No associated systemic symptoms reported. The patient indicates burning, enlargement and itching. The patient is 18–29, female. The photograph is a close-up of the affected area. The patient considered this a rash. The patient indicates the condition has been present for about one day. Texture is reported as raised or bumpy. Located on the arm, head or neck, top or side of the foot, front of the torso, back of the hand and leg: 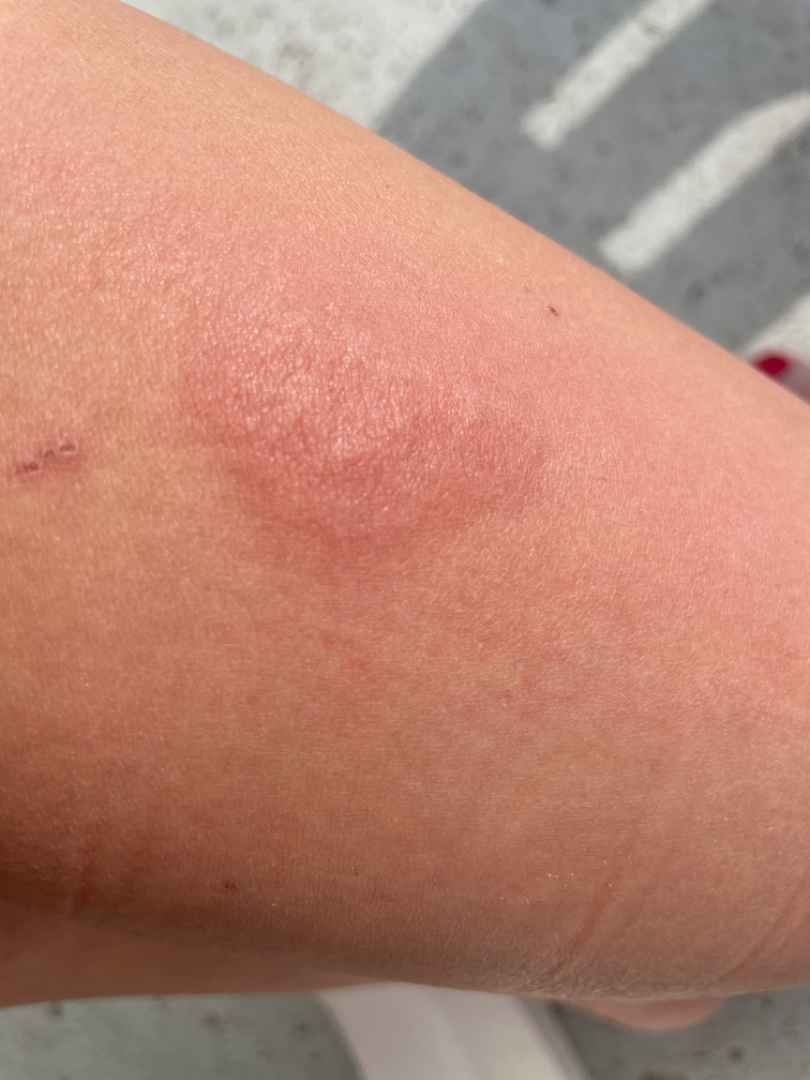The skin findings could not be characterized from the image.